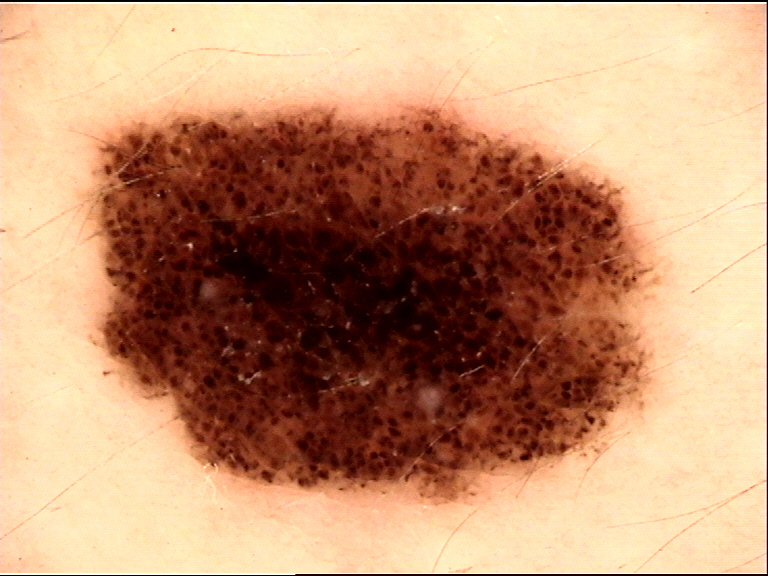image = dermatoscopy
diagnostic label = dysplastic compound nevus (expert consensus)